A dermoscopic image of a skin lesion.
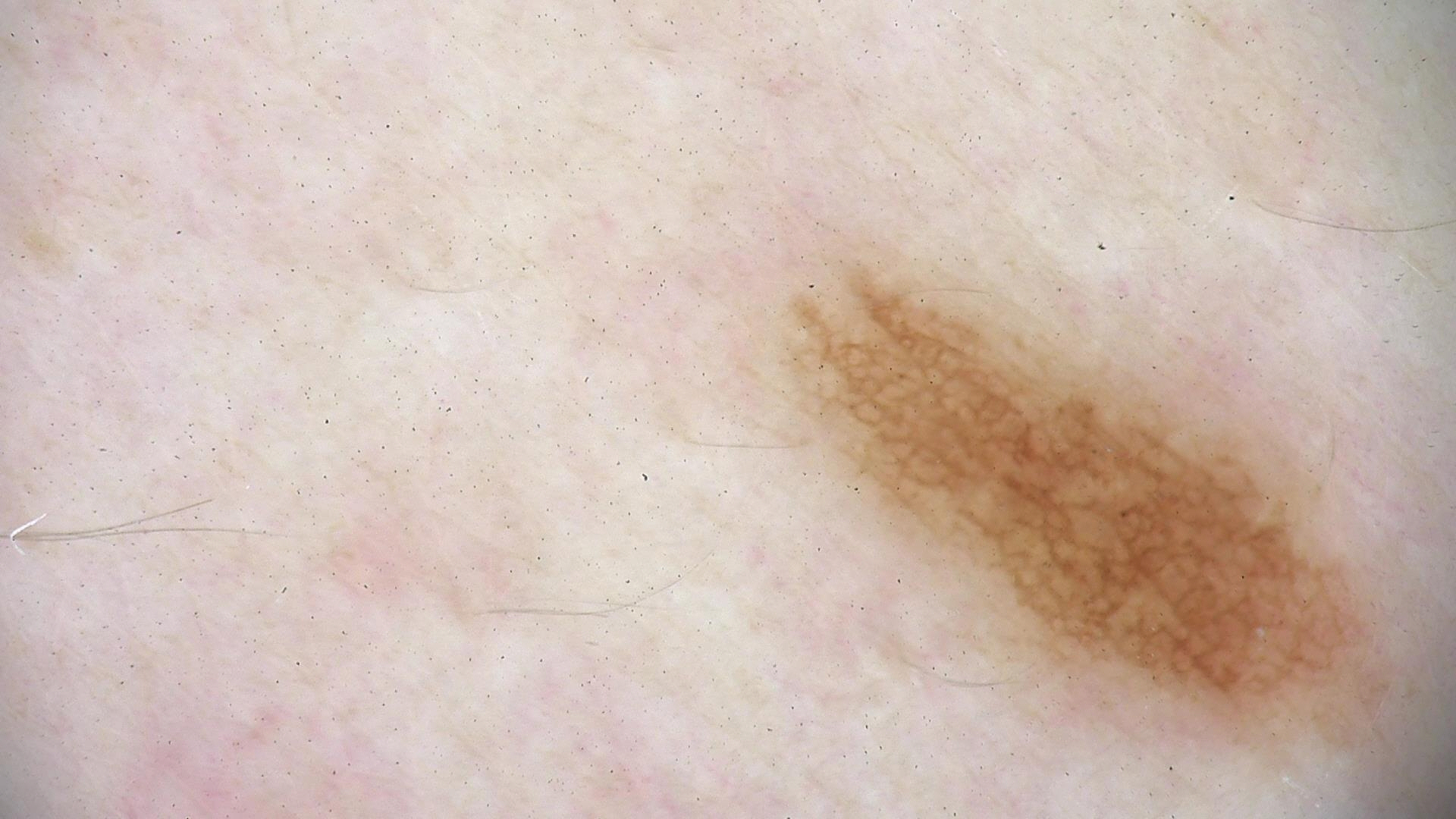Labeled as a dysplastic junctional nevus.